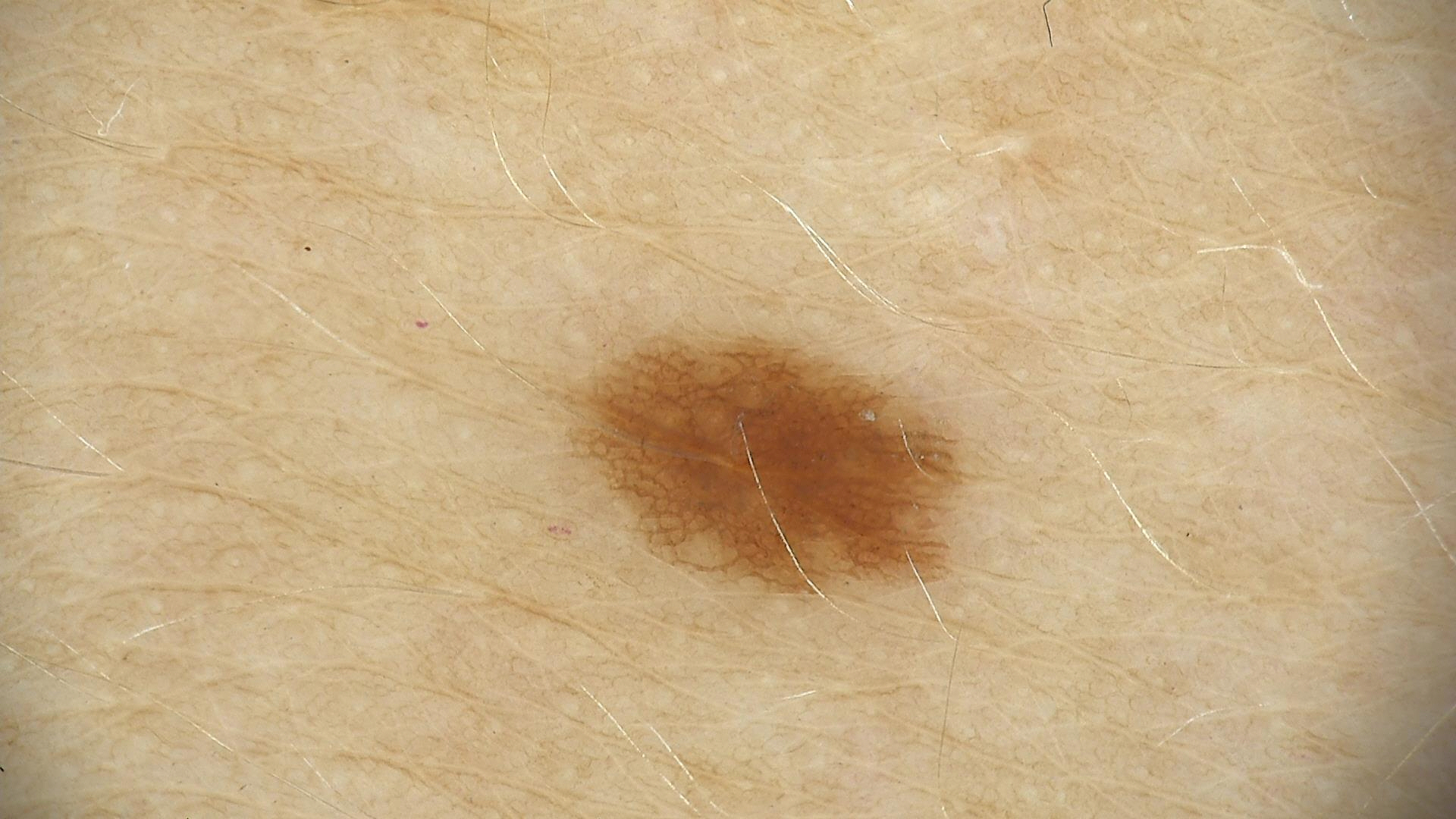Case:
• diagnosis · junctional nevus (expert consensus)